Fitzpatrick phototype II · this image was taken at a distance.
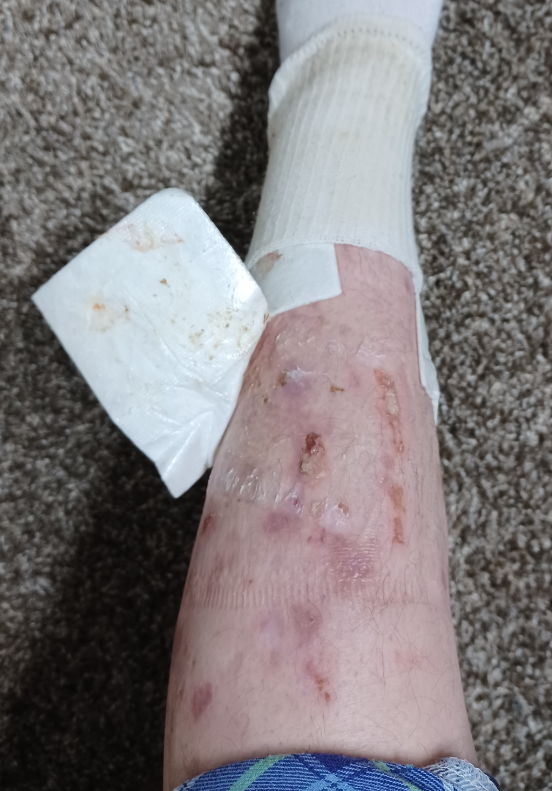The skin findings could not be characterized from the image.